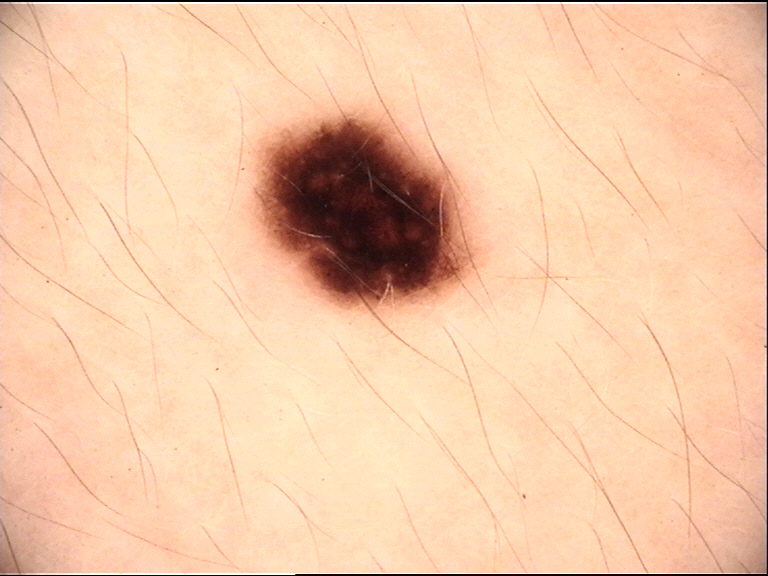Classified as a junctional nevus.